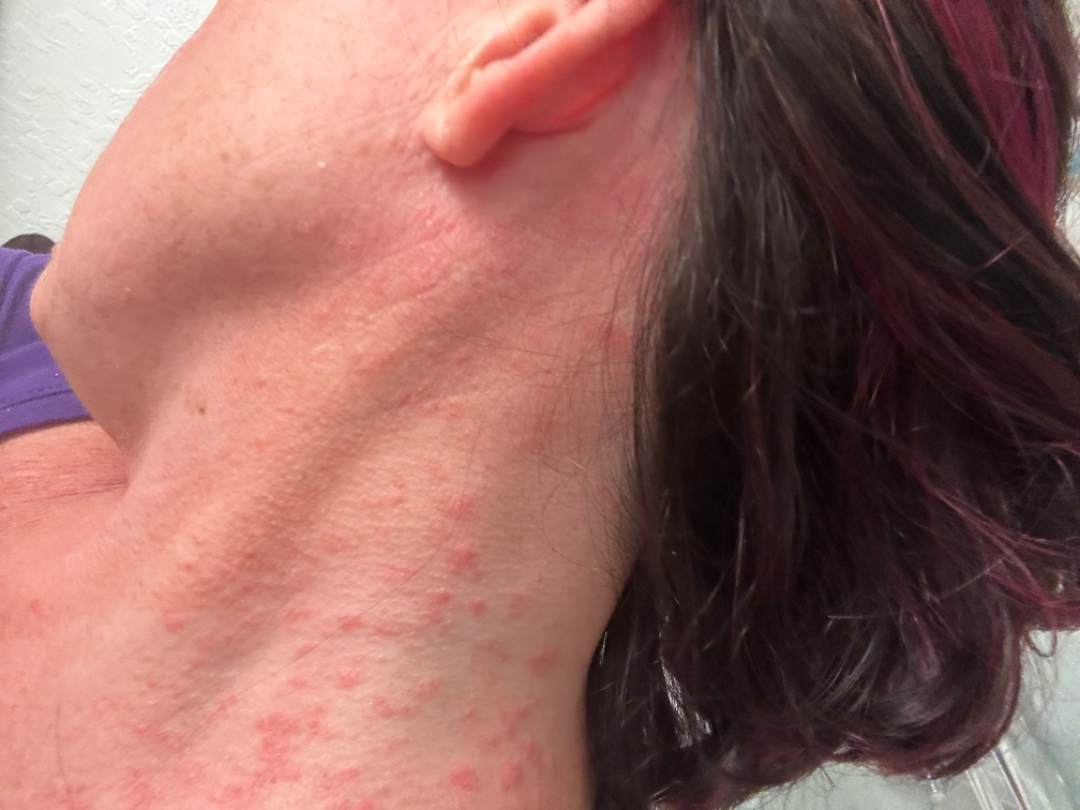Notes:
– site — front of the torso, arm, back of the torso, head or neck and leg
– shot type — close-up
– differential — Urticaria; Acute dermatitis, NOS; and Allergic Contact Dermatitis were considered with similar weight